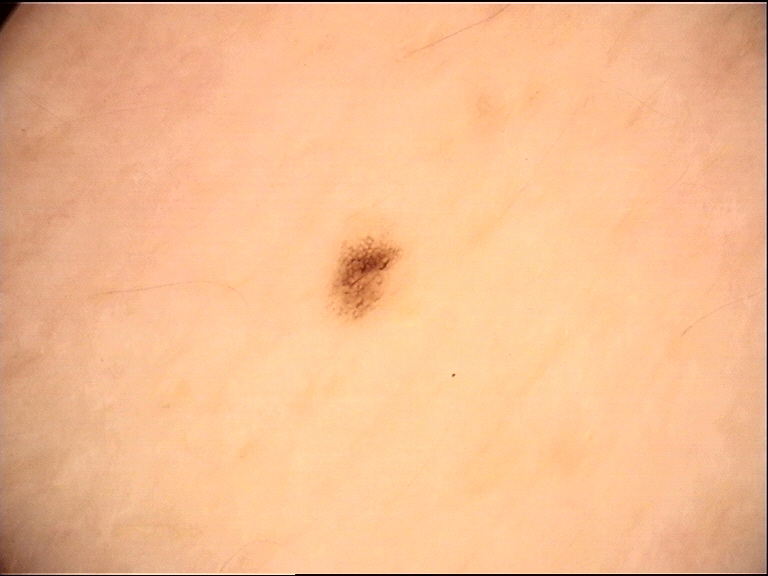diagnosis: dysplastic junctional nevus (expert consensus).